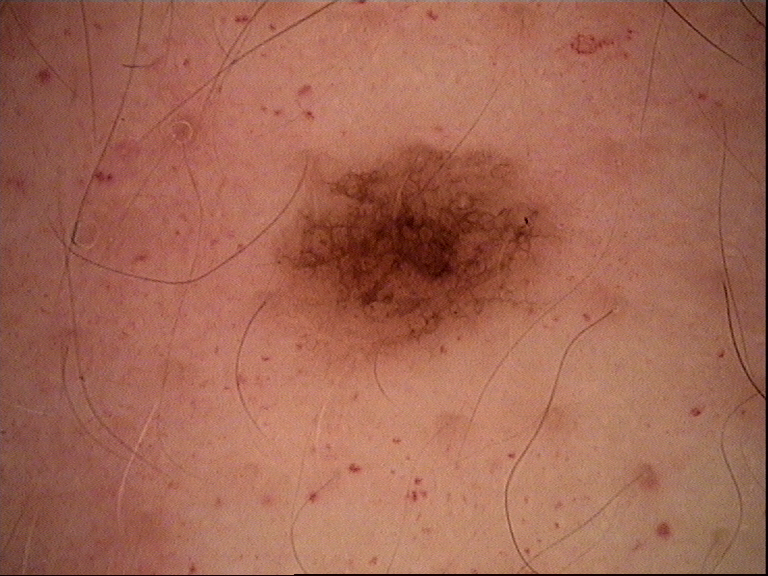Dermoscopy of a skin lesion. The diagnosis was a dysplastic junctional nevus.